A dermoscopic close-up of a skin lesion: 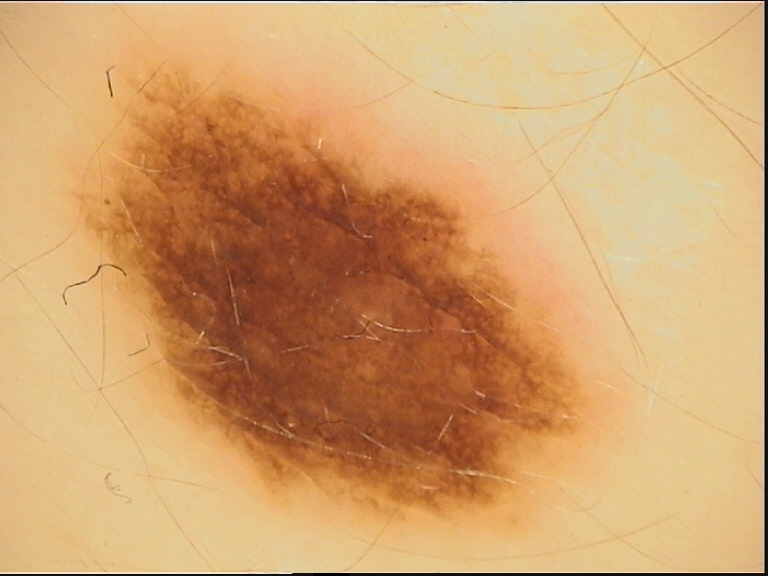class: dysplastic junctional nevus (expert consensus).